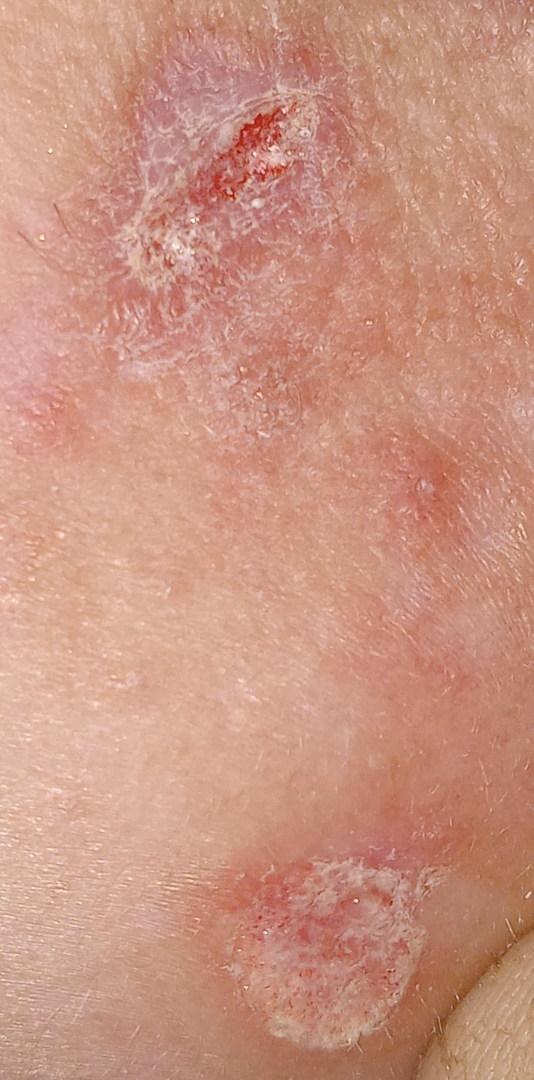Q: What was the assessment?
A: not assessable